Collected as part of a research study, without a referral diagnosis; a skin lesion imaged with a dermatoscope; by self-report, a personal history of skin cancer and a personal history of cancer; a female subject aged 71; the patient says their skin reddens with sun exposure: 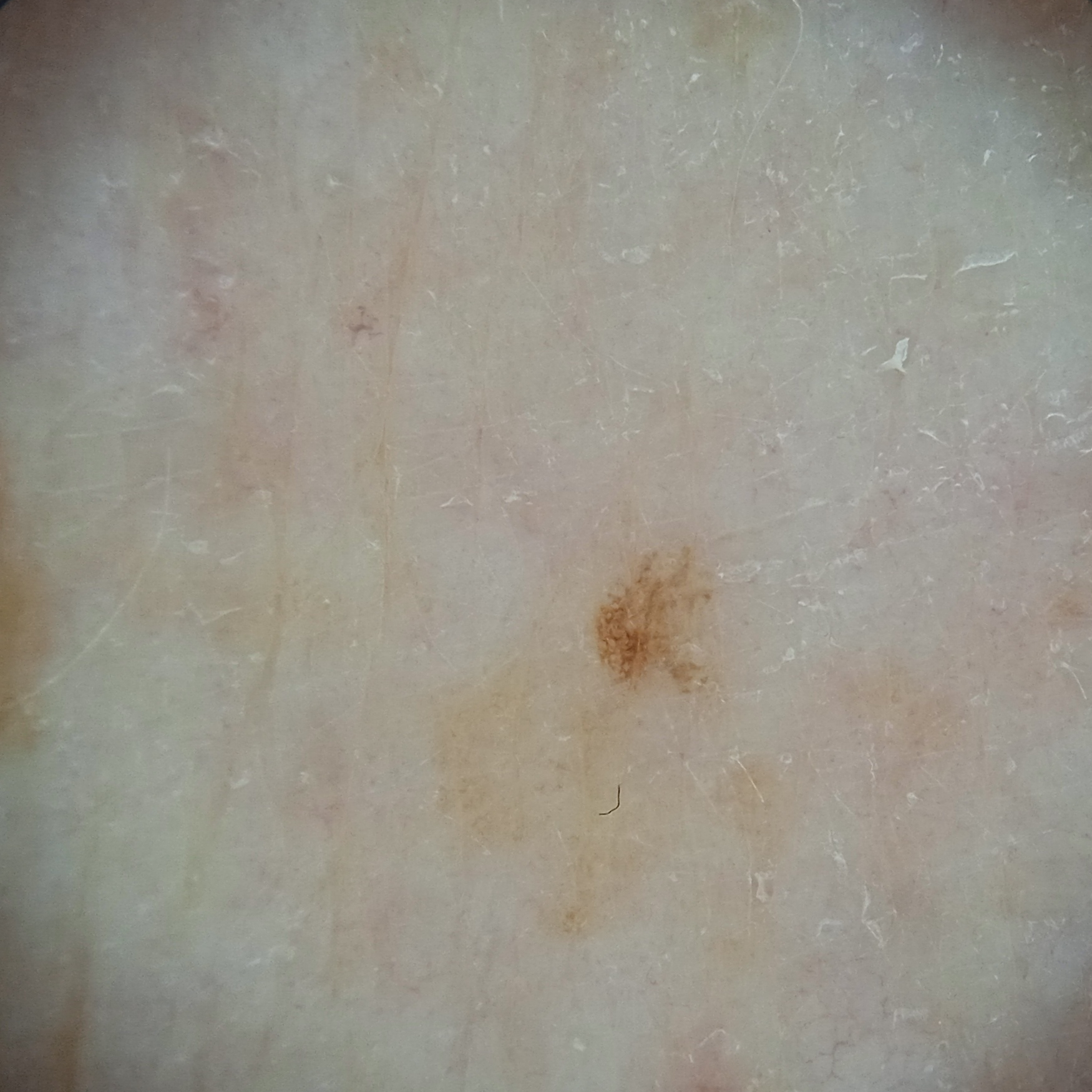Findings: The lesion is on an arm. The lesion is about 1.7 mm across. Conclusion: Dermatologist review favored a melanocytic nevus.